Located on the leg and arm. Self-categorized by the patient as a rash. Female subject, age 18–29. The patient reports the condition has been present for one to four weeks. Texture is reported as raised or bumpy and rough or flaky. A close-up photograph. The patient reported no systemic symptoms. The patient reports burning, itching, enlargement, pain and bothersome appearance — 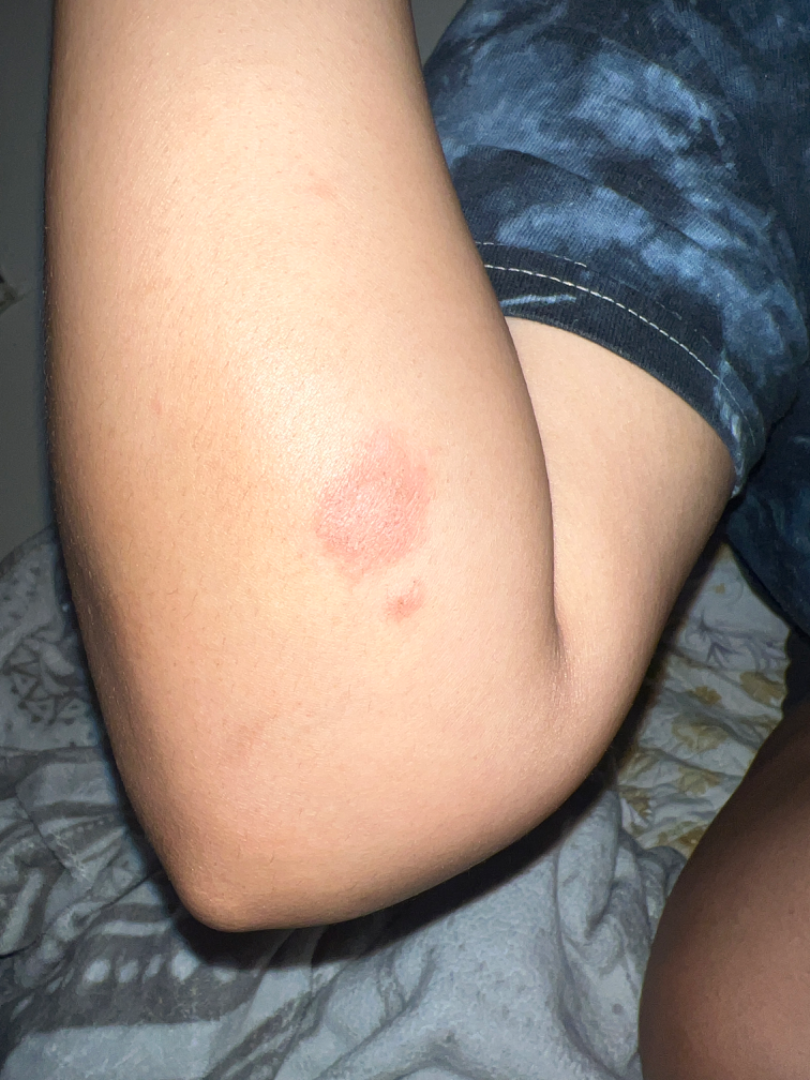Q: What was the assessment?
A: indeterminate from the photograph